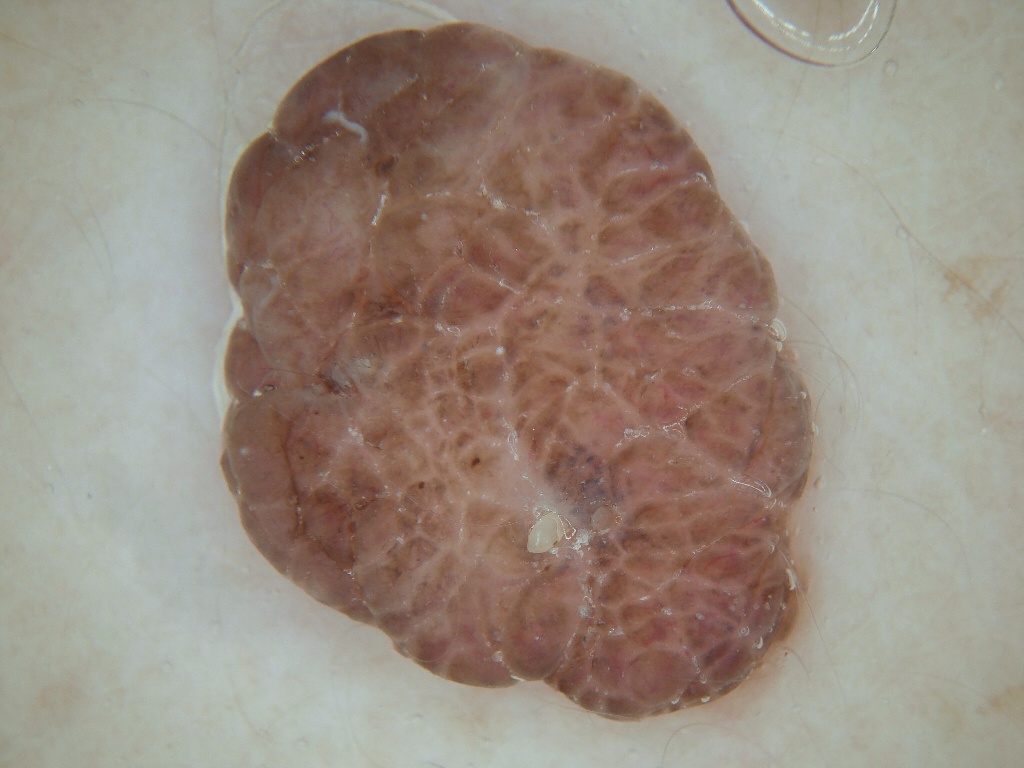Case summary: This is a dermoscopic photograph of a skin lesion. As (left, top, right, bottom), the lesion occupies the region 220/22/811/717. Conclusion: Clinically diagnosed as a melanocytic nevus.